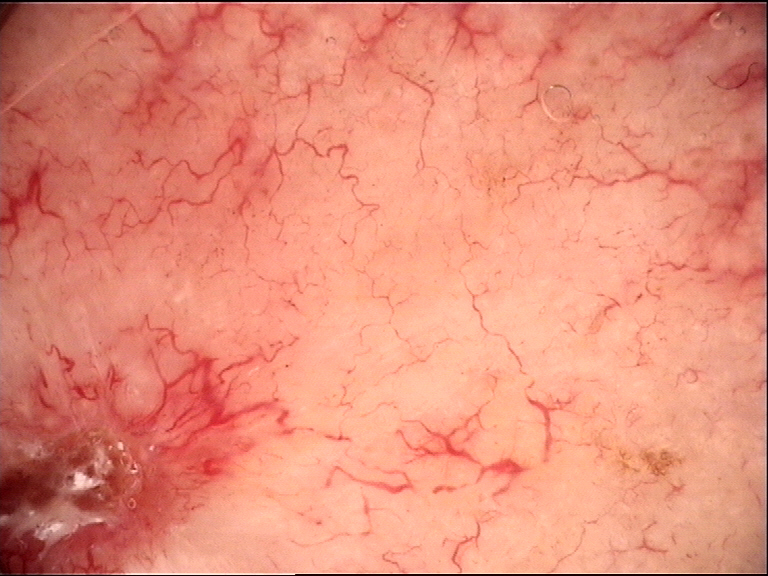{"image": "dermatoscopy", "diagnosis": {"name": "basal cell carcinoma", "code": "bcc", "malignancy": "malignant", "super_class": "non-melanocytic", "confirmation": "histopathology"}}